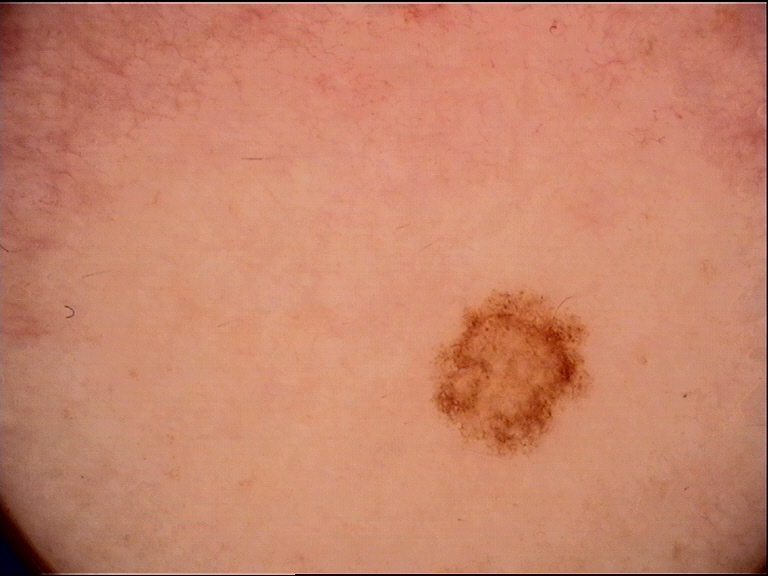Case:
* assessment: dysplastic junctional nevus (expert consensus)